A dermoscopic image of a skin lesion · the patient is a male in their mid- to late 40s:
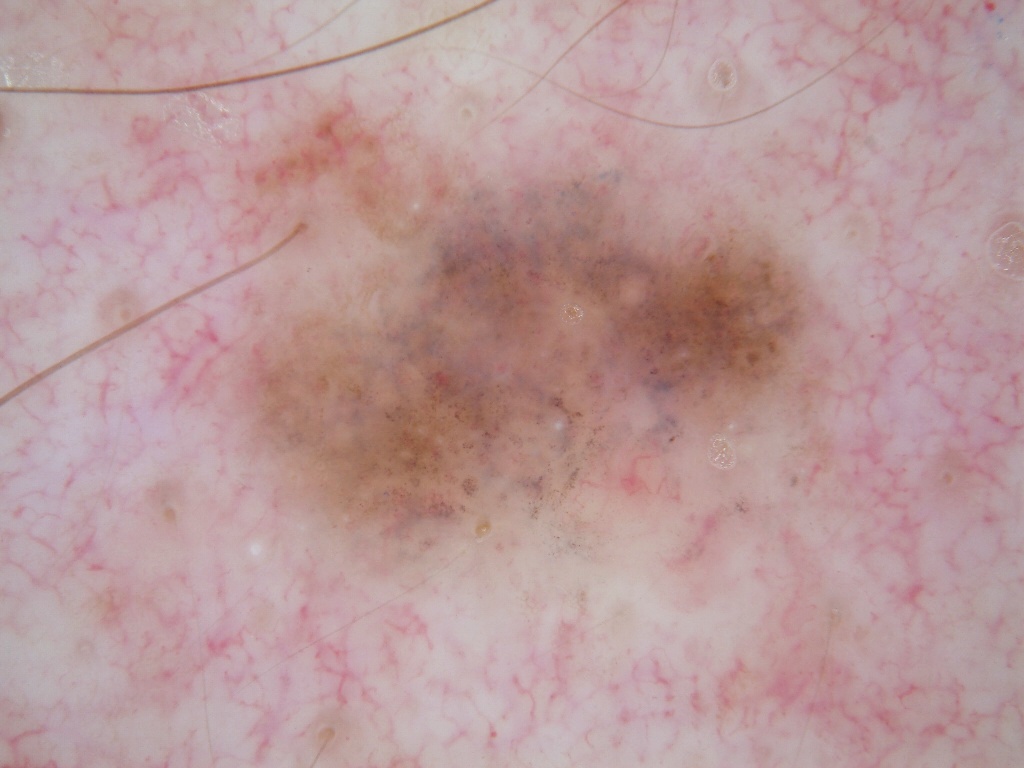lesion_location:
  bbox_xyxy:
    - 220
    - 80
    - 843
    - 608
dermoscopic_features:
  present:
    - milia-like cysts
  absent:
    - negative network
    - streaks
    - globules
    - pigment network
diagnosis:
  name: melanoma
  malignancy: malignant
  lineage: melanocytic
  provenance: histopathology